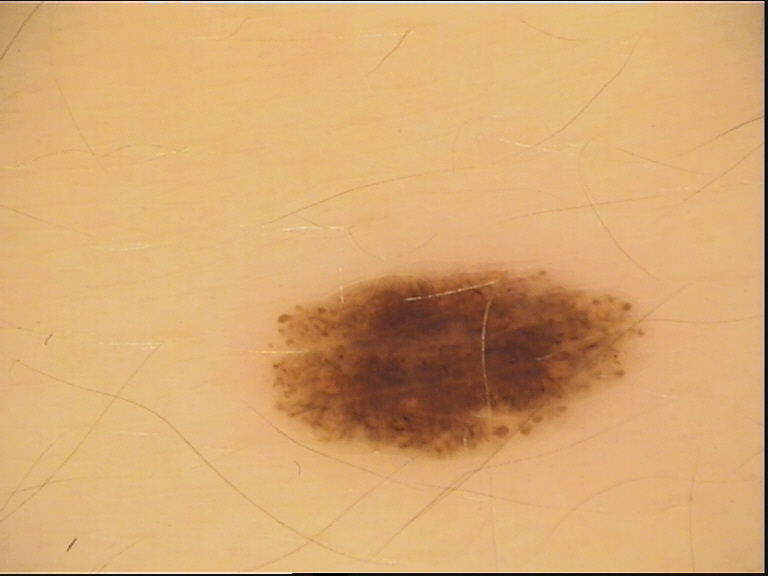Findings: A dermoscopy image of a single skin lesion. Conclusion: The diagnostic label was a dysplastic junctional nevus.